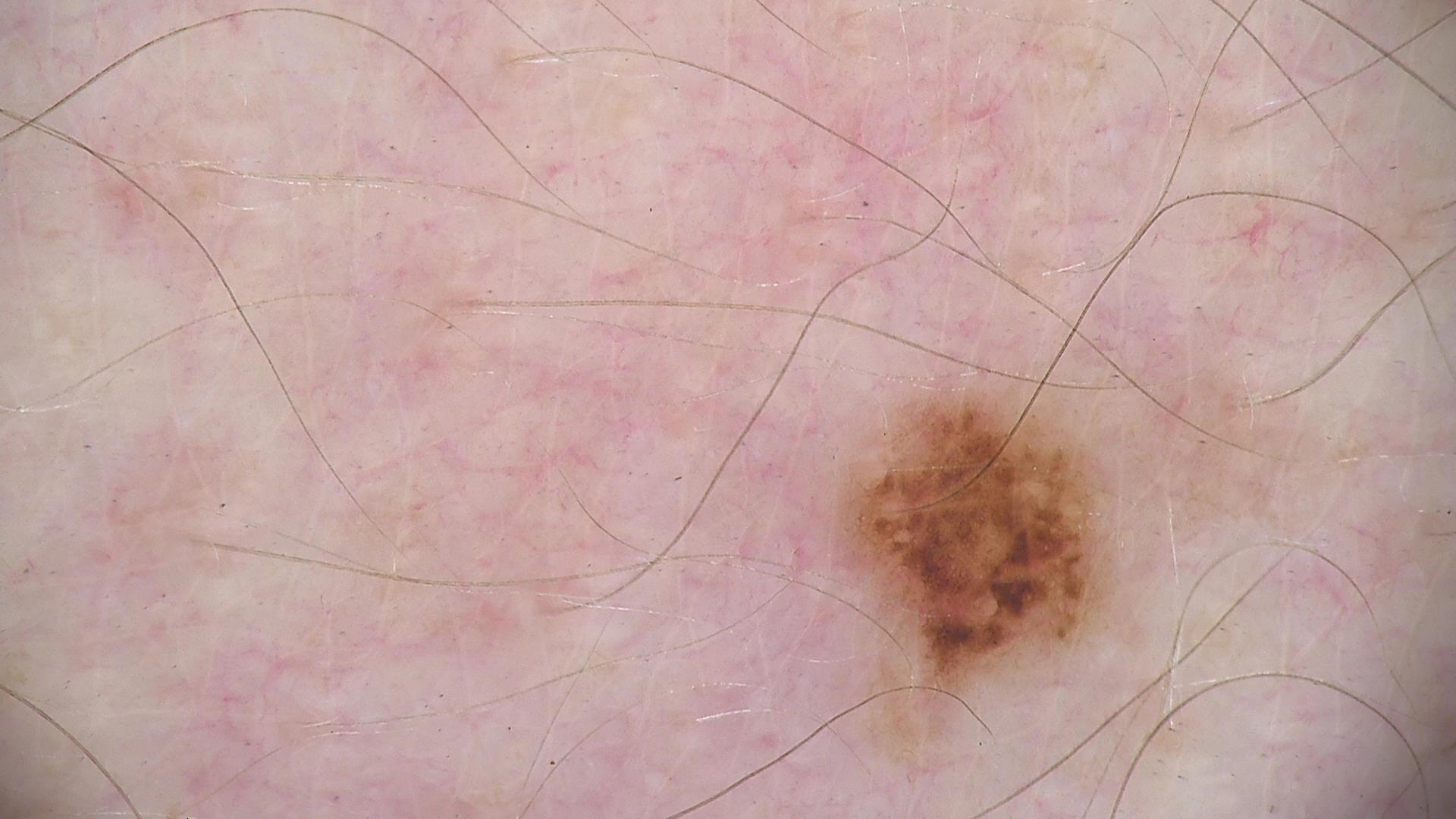Dermoscopy of a skin lesion.
Classified as a benign lesion — a dysplastic junctional nevus.